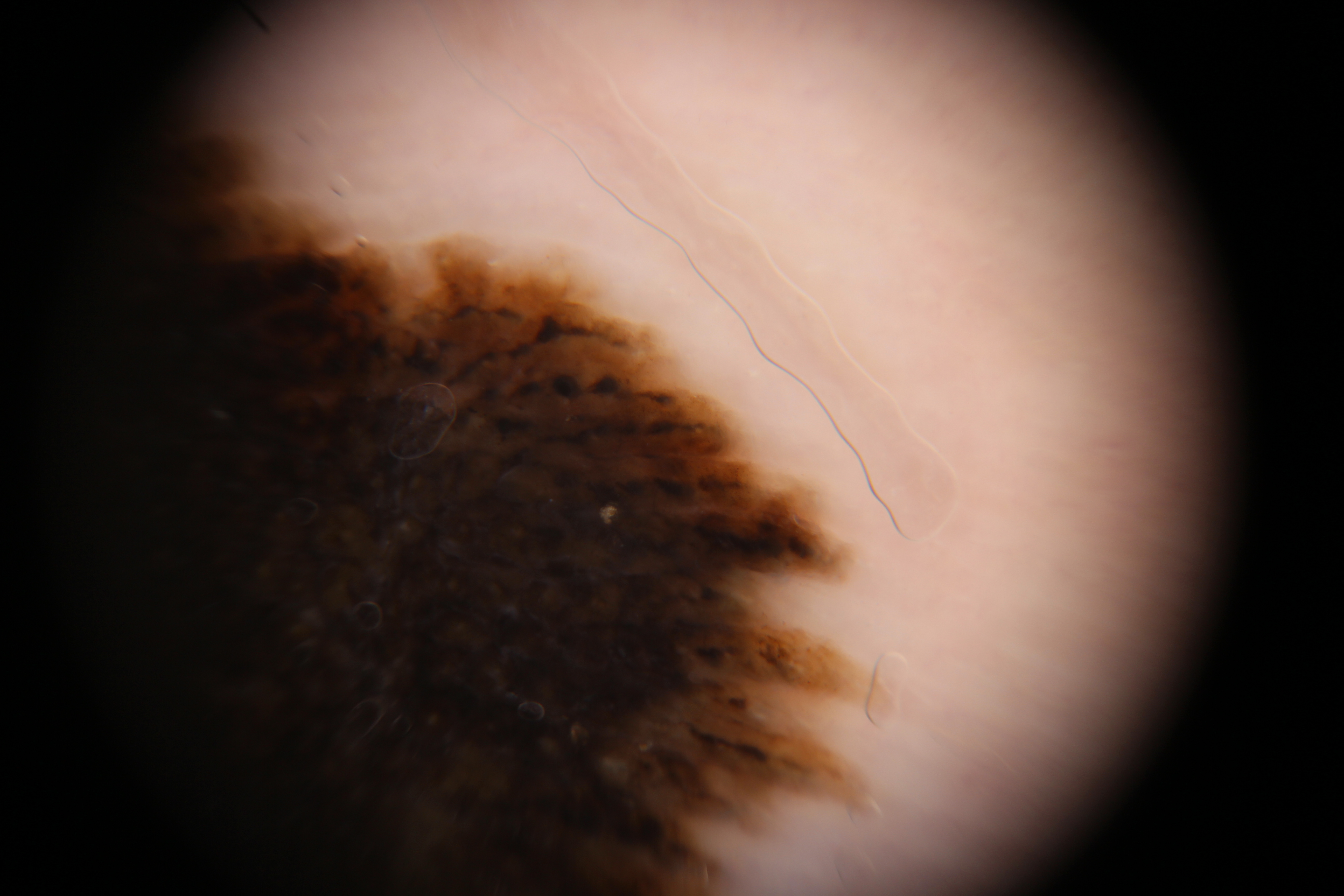Diagnosis: Confirmed on histopathology as an acral lentiginous melanoma.